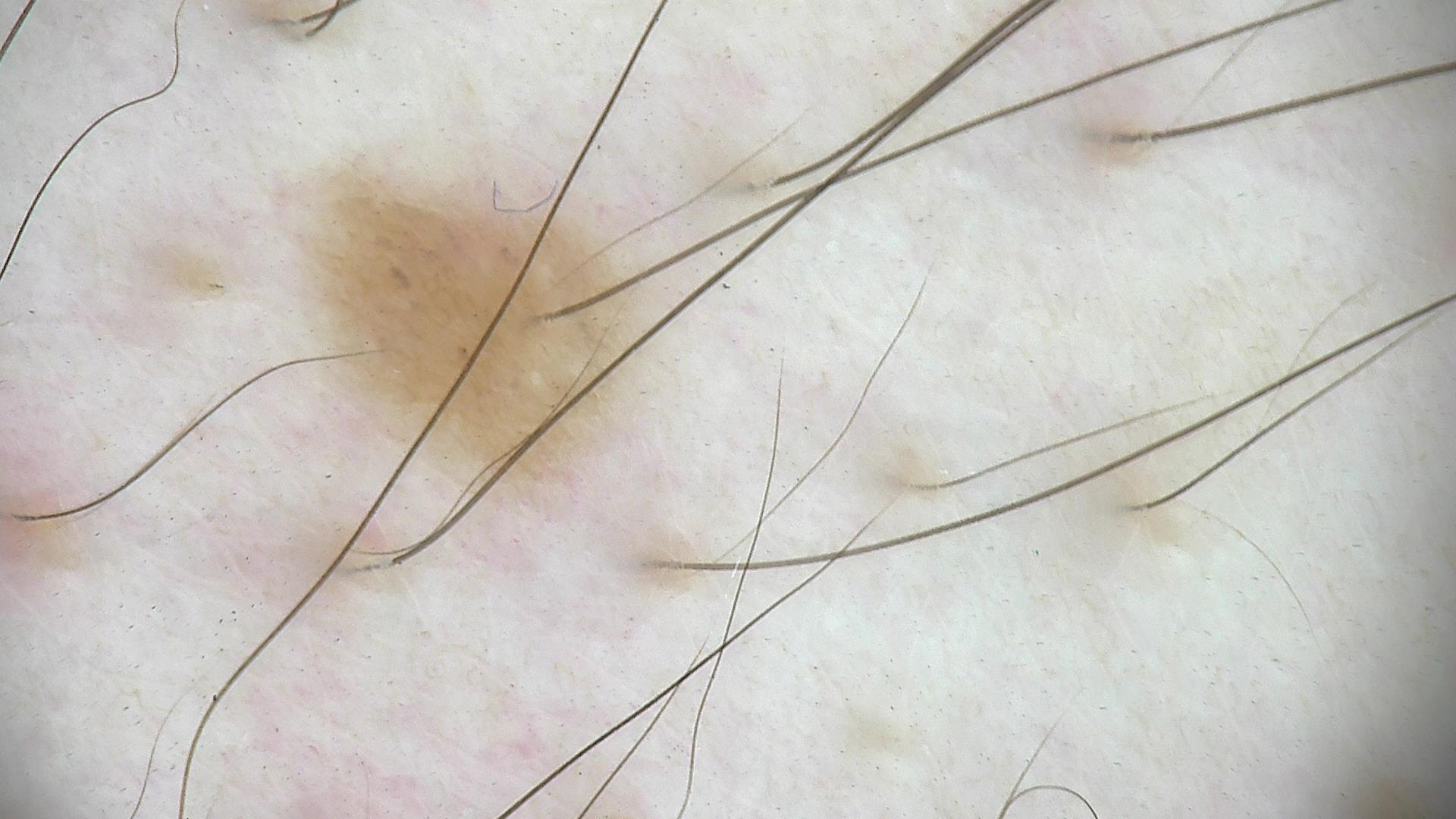| key | value |
|---|---|
| image | dermatoscopy |
| label | dysplastic junctional nevus (expert consensus) |